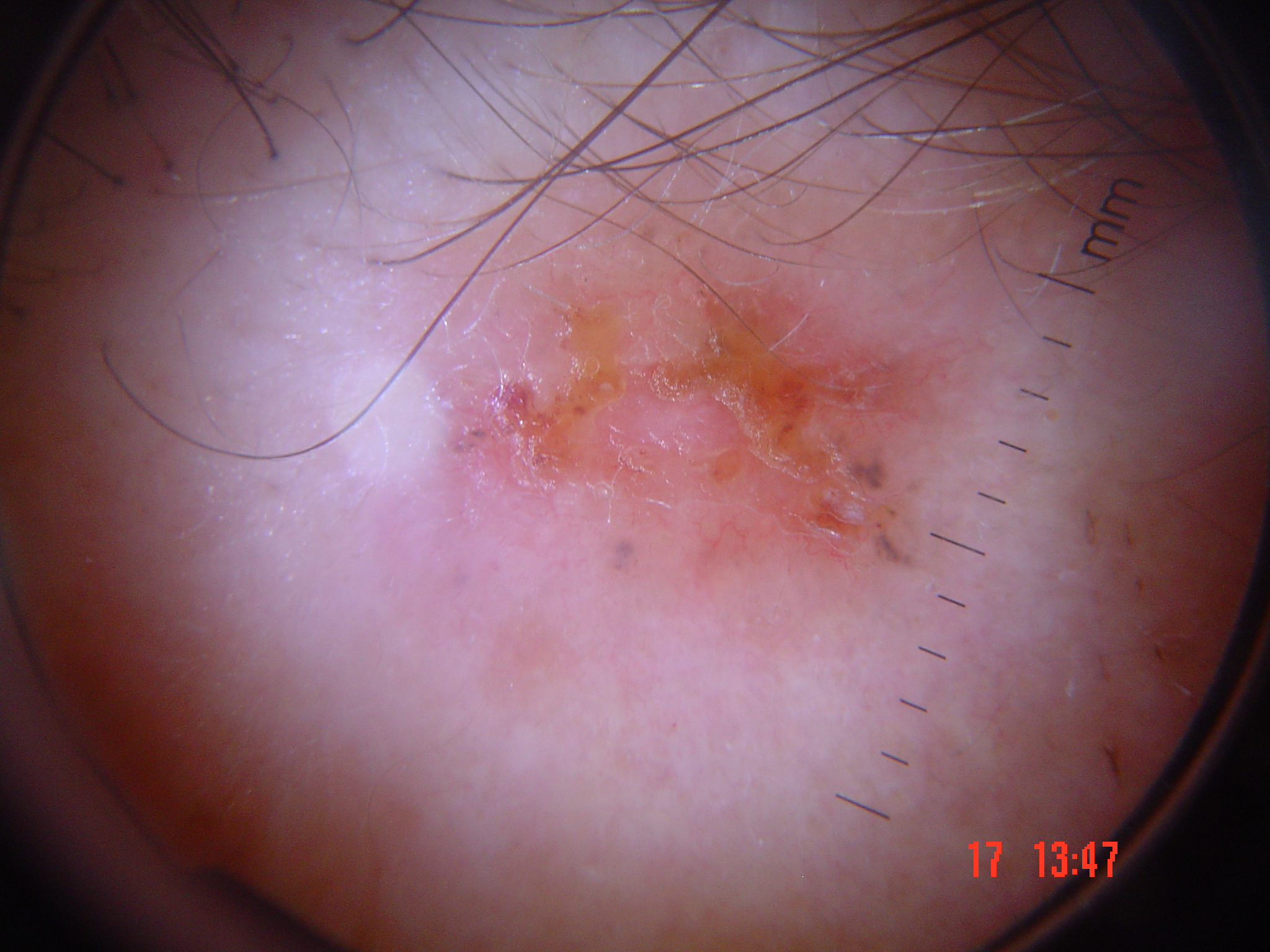The biopsy diagnosis was a basal cell carcinoma.